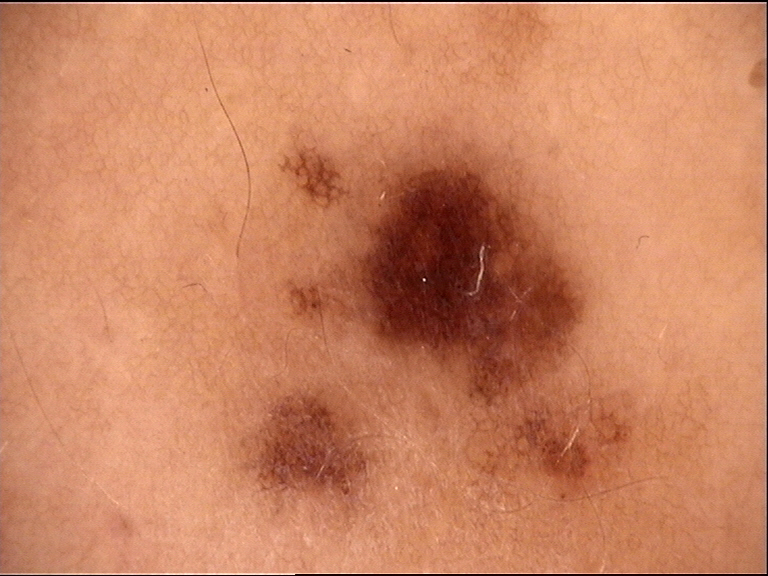The diagnostic label was a dysplastic junctional nevus.